The patient considered this a rash. The lesion is described as raised or bumpy. The photo was captured at a distance. The contributor is 30–39, male. Skin tone: FST I; lay graders estimated Monk Skin Tone 1–2. The contributor reports the condition has been present for less than one week. The affected area is the head or neck. Symptoms reported: pain, burning and itching — 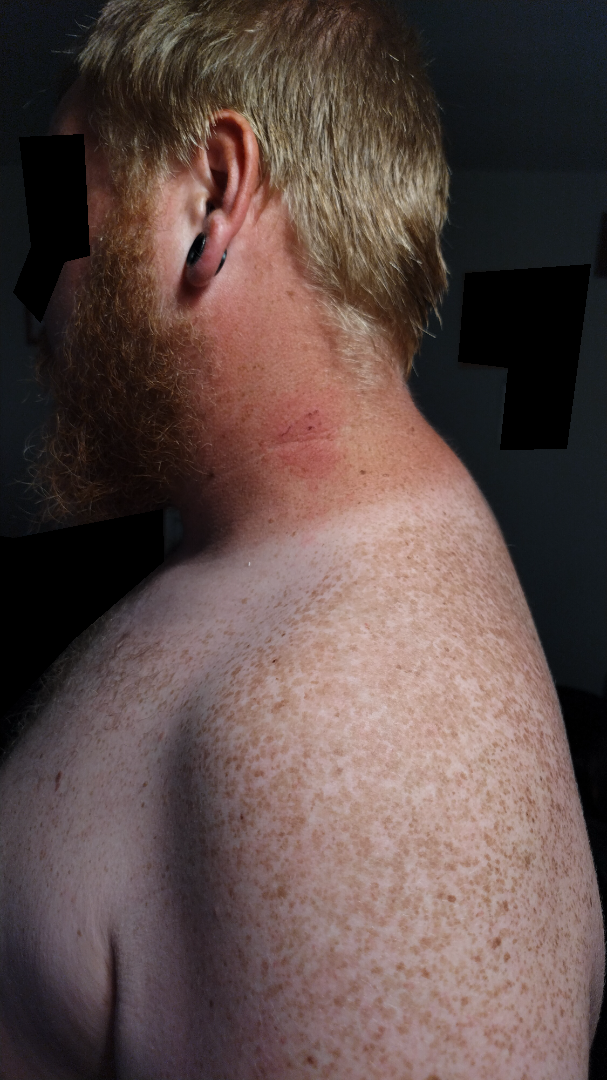Q: What is the dermatologist's impression?
A: most likely Allergic Contact Dermatitis